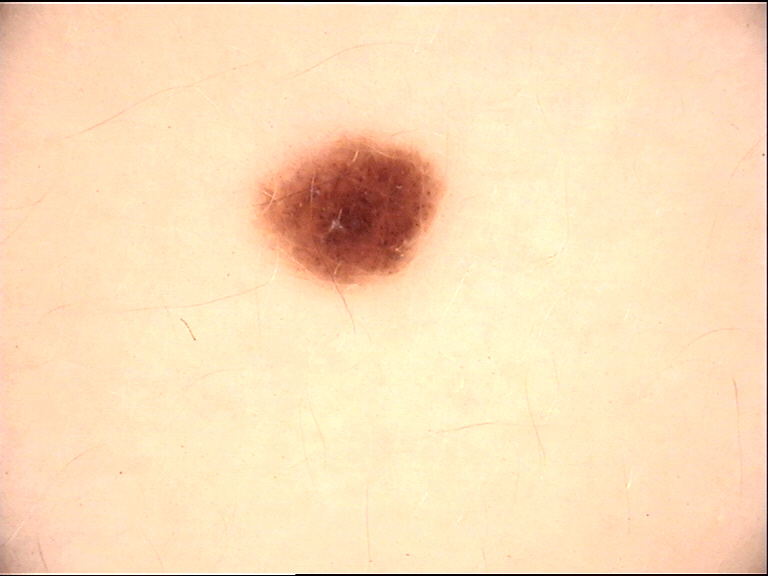The diagnosis was a dysplastic junctional nevus.